Texture is reported as rough or flaky · a close-up photograph — 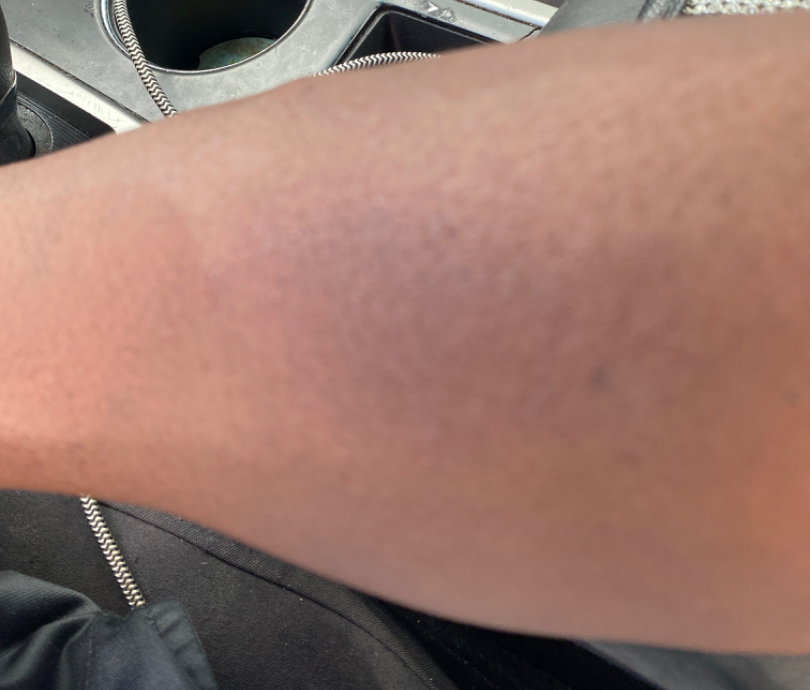Q: What was the assessment?
A: not assessable